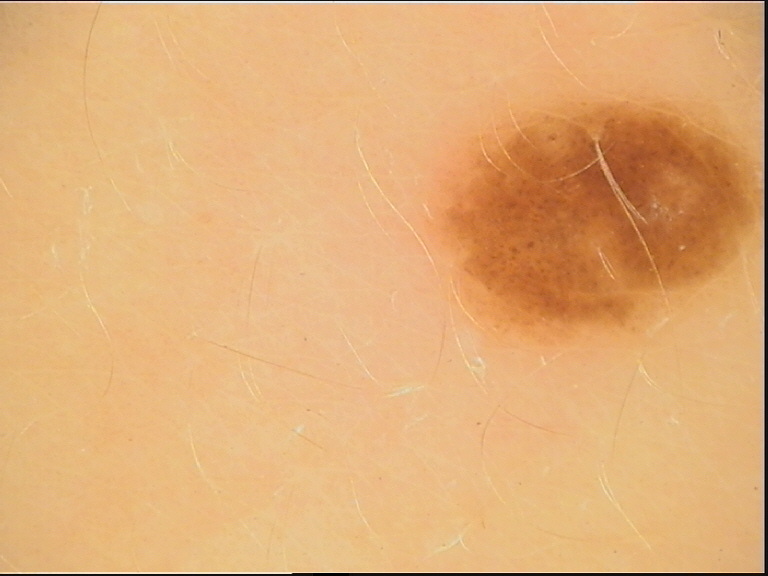A dermatoscopic image of a skin lesion. The diagnostic label was a dysplastic junctional nevus.